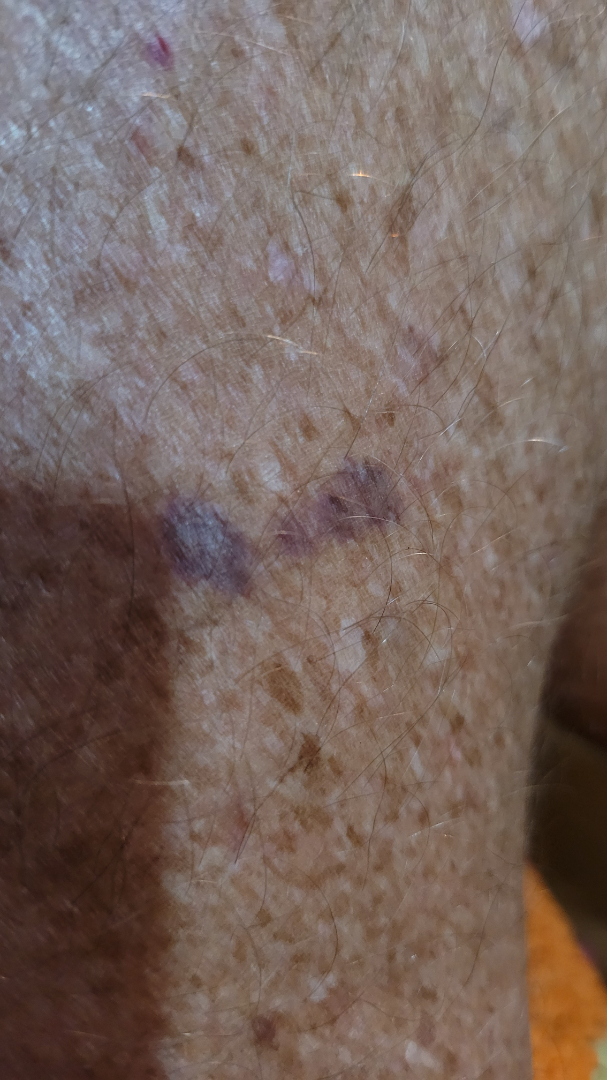| field | value |
|---|---|
| assessment | could not be assessed |